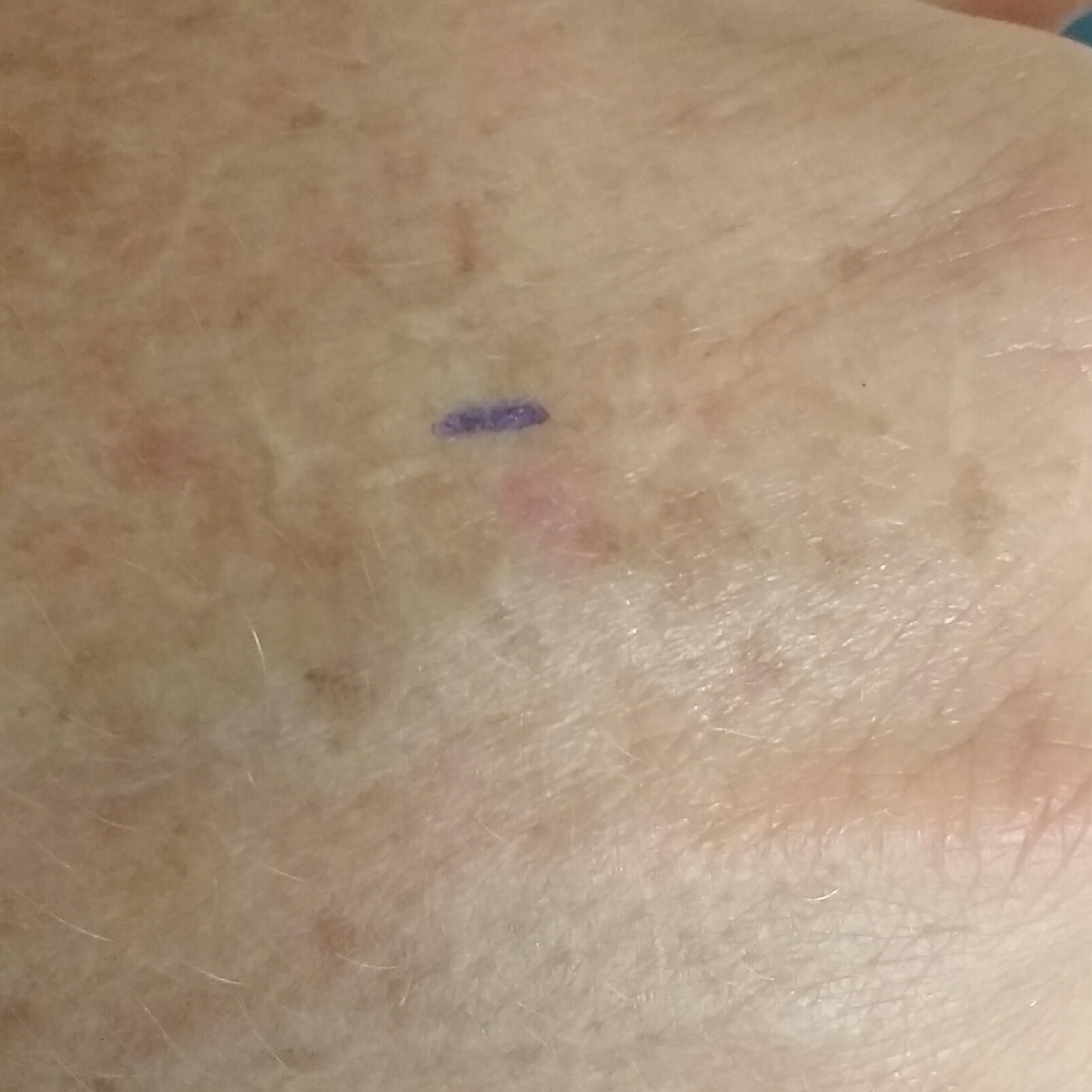Summary: A clinical photograph showing a skin lesion. The lesion involves a forearm. By the patient's account, the lesion is elevated. Impression: The consensus clinical diagnosis was an actinic keratosis.